This image was taken at a distance. The top or side of the foot is involved. The patient is 18–29, female.
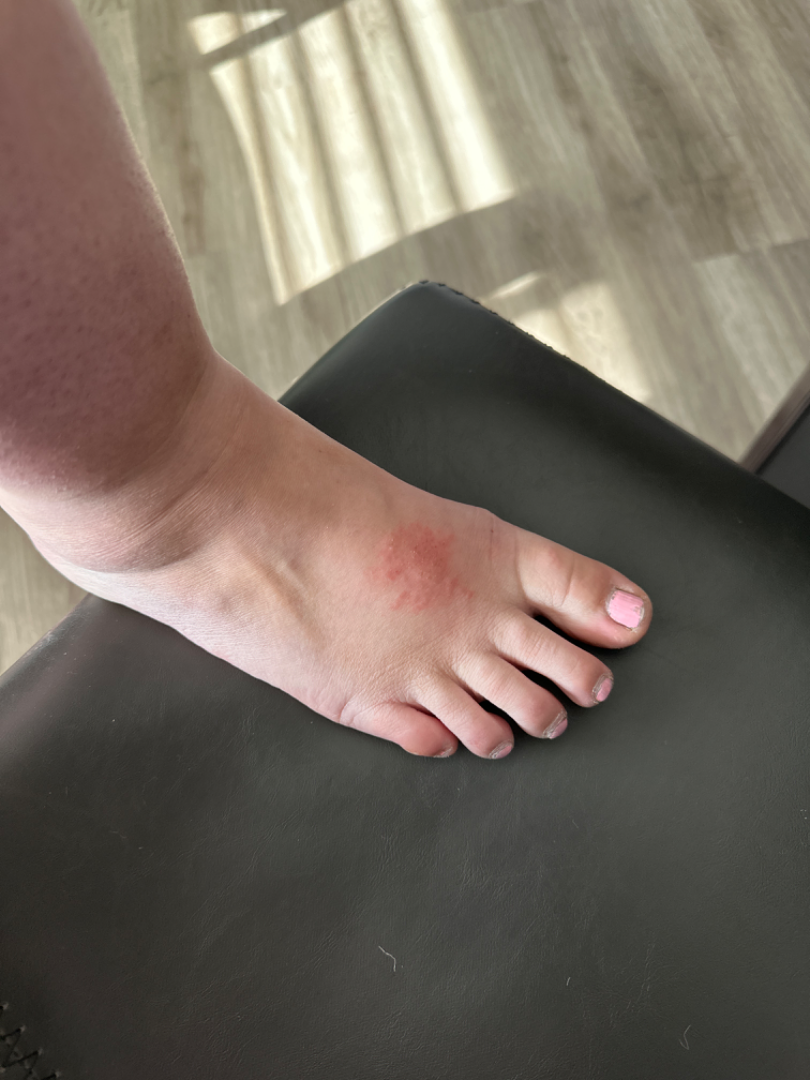The patient indicates the lesion is raised or bumpy. The patient indicates itching. The patient considered this a rash. On photographic review, most consistent with Allergic Contact Dermatitis.